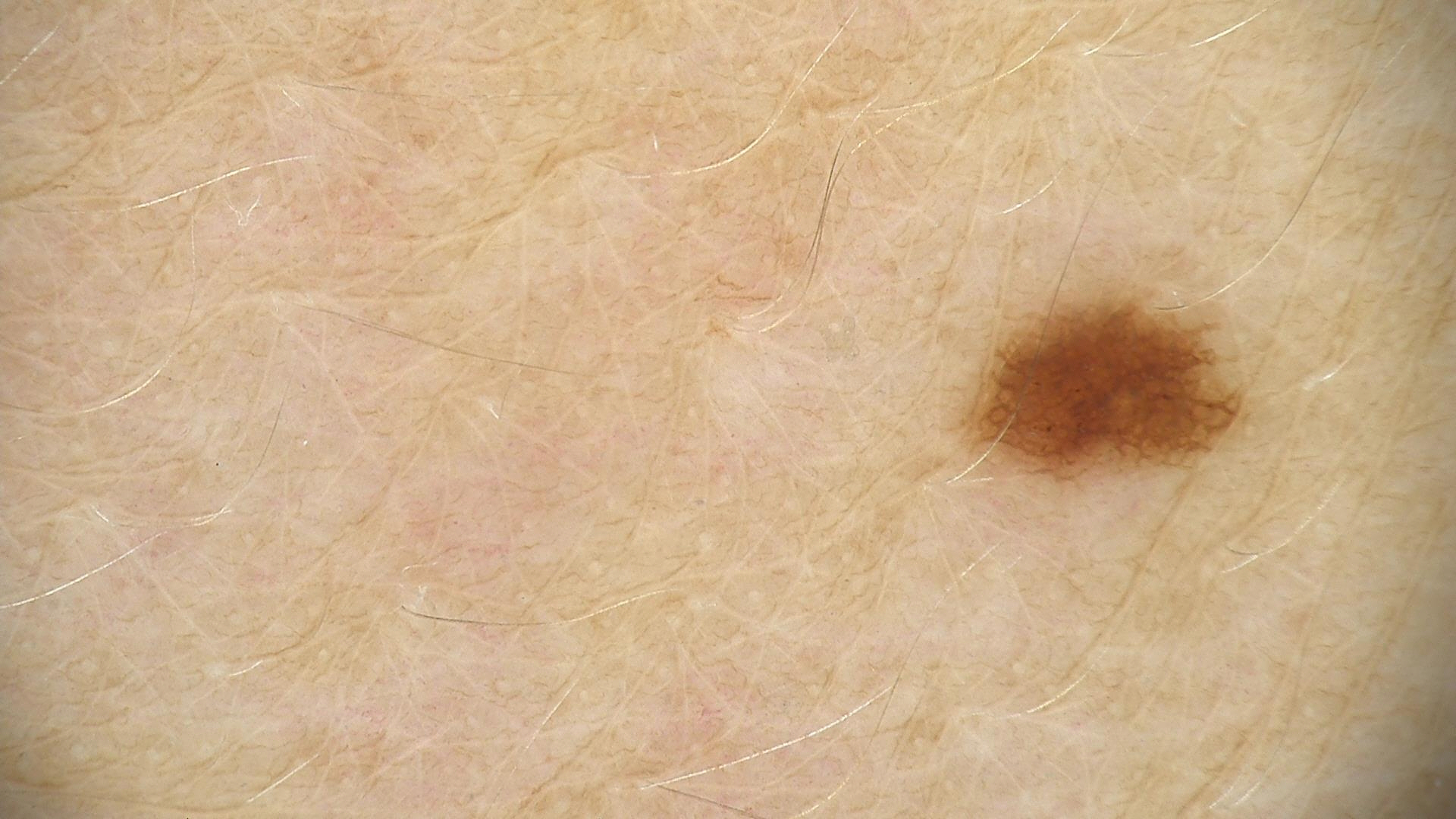Summary:
A dermoscopic image of a skin lesion.
Impression:
Consistent with a banal lesion — a junctional nevus.